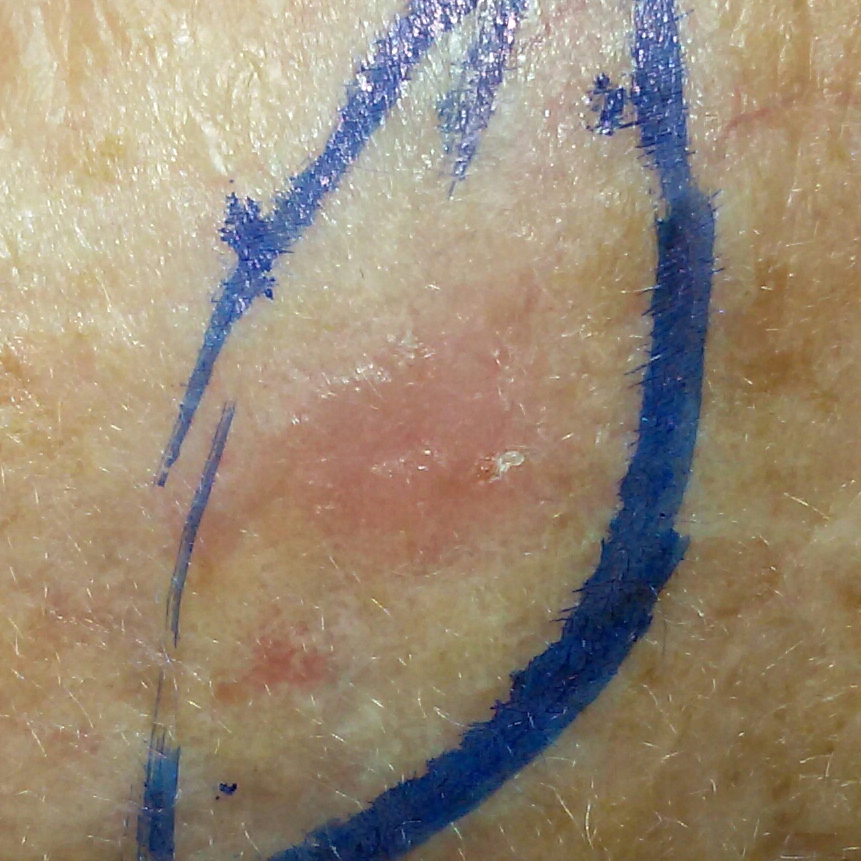A female subject in their 80s.
A clinical photo of a skin lesion taken with a smartphone.
By the patient's account, the lesion is elevated and itches, but does not hurt.
Histopathological examination showed a basal cell carcinoma.